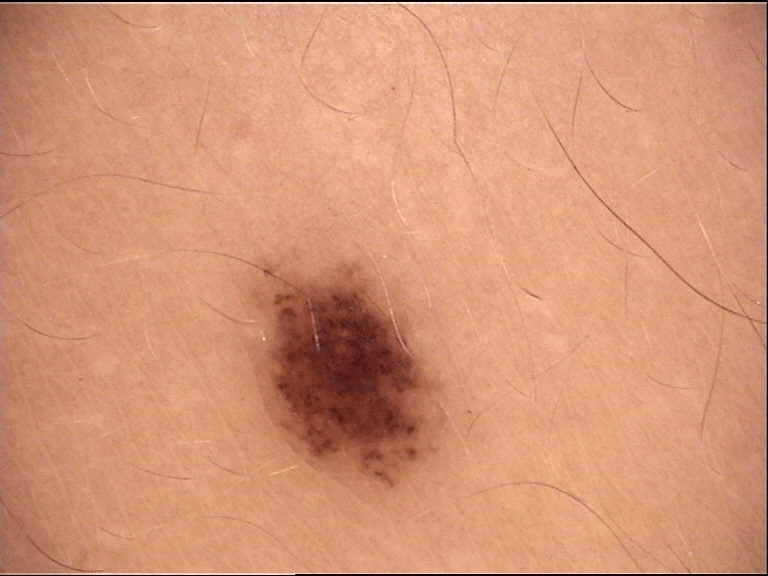A dermoscopic photograph of a skin lesion.
The diagnostic label was a benign lesion — a dysplastic compound nevus.